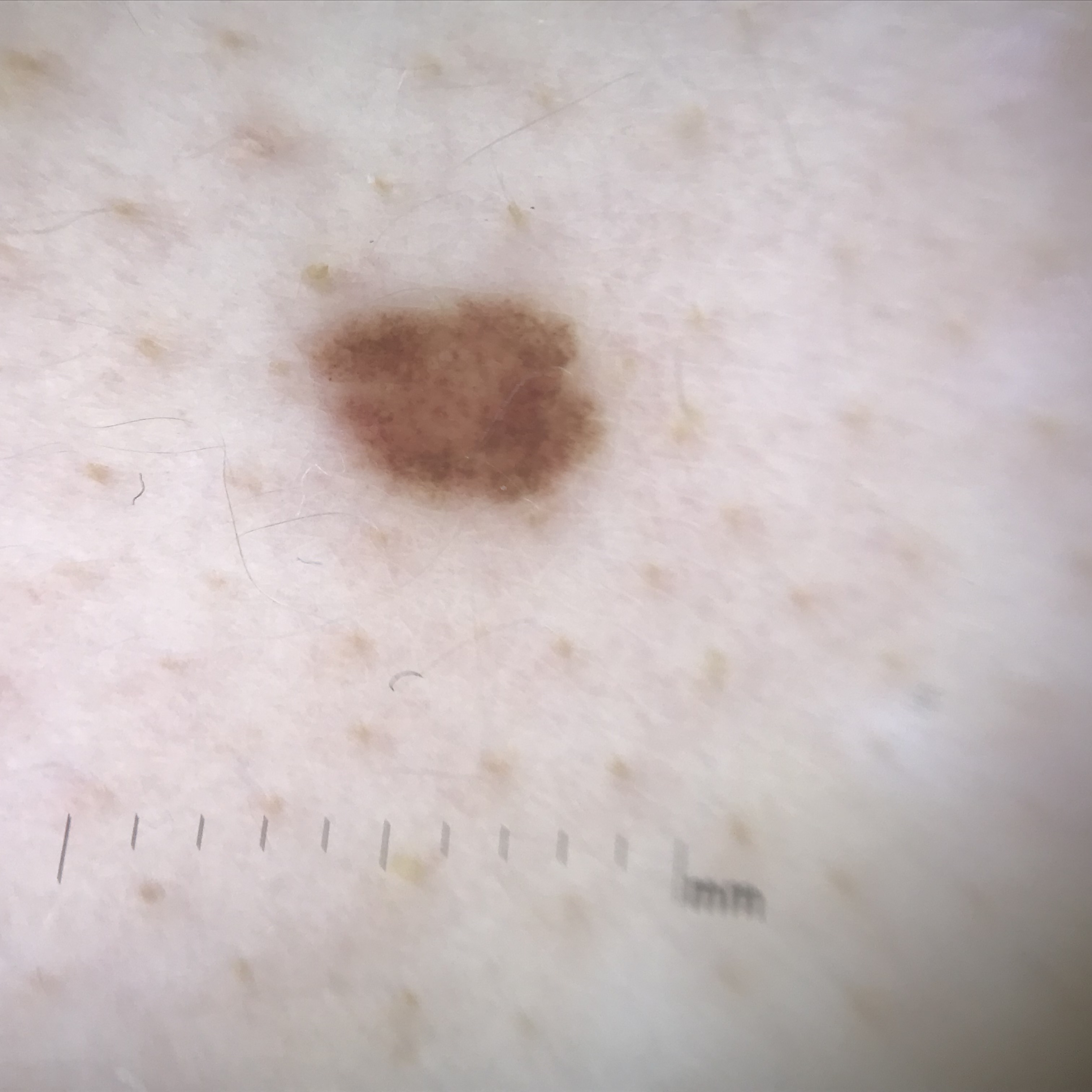Case:
* label — dysplastic junctional nevus (expert consensus)